A female patient aged around 35 — 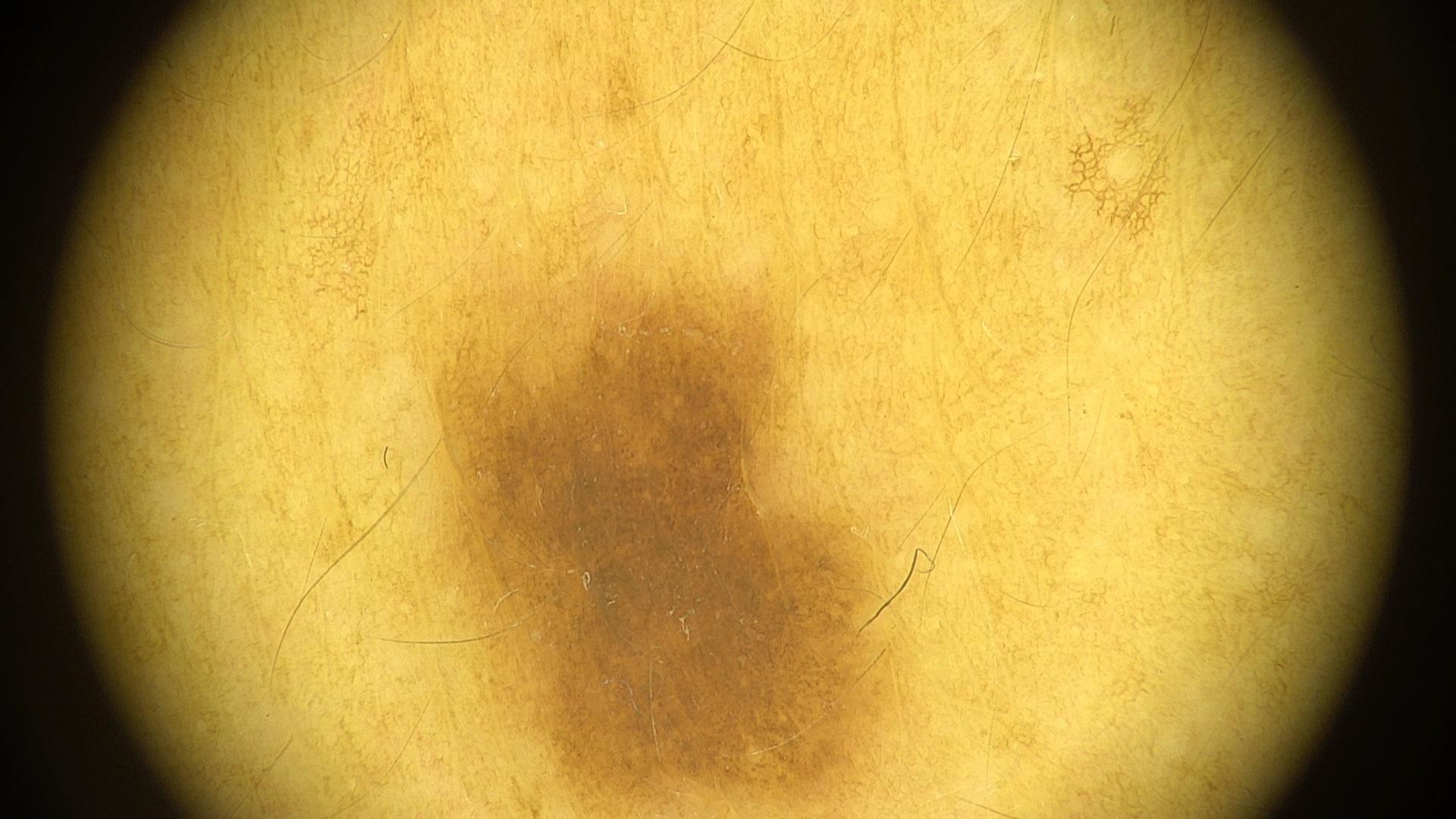Q: What is the anatomic site?
A: the trunk
Q: What is the diagnosis?
A: Nevus (clinical impression)